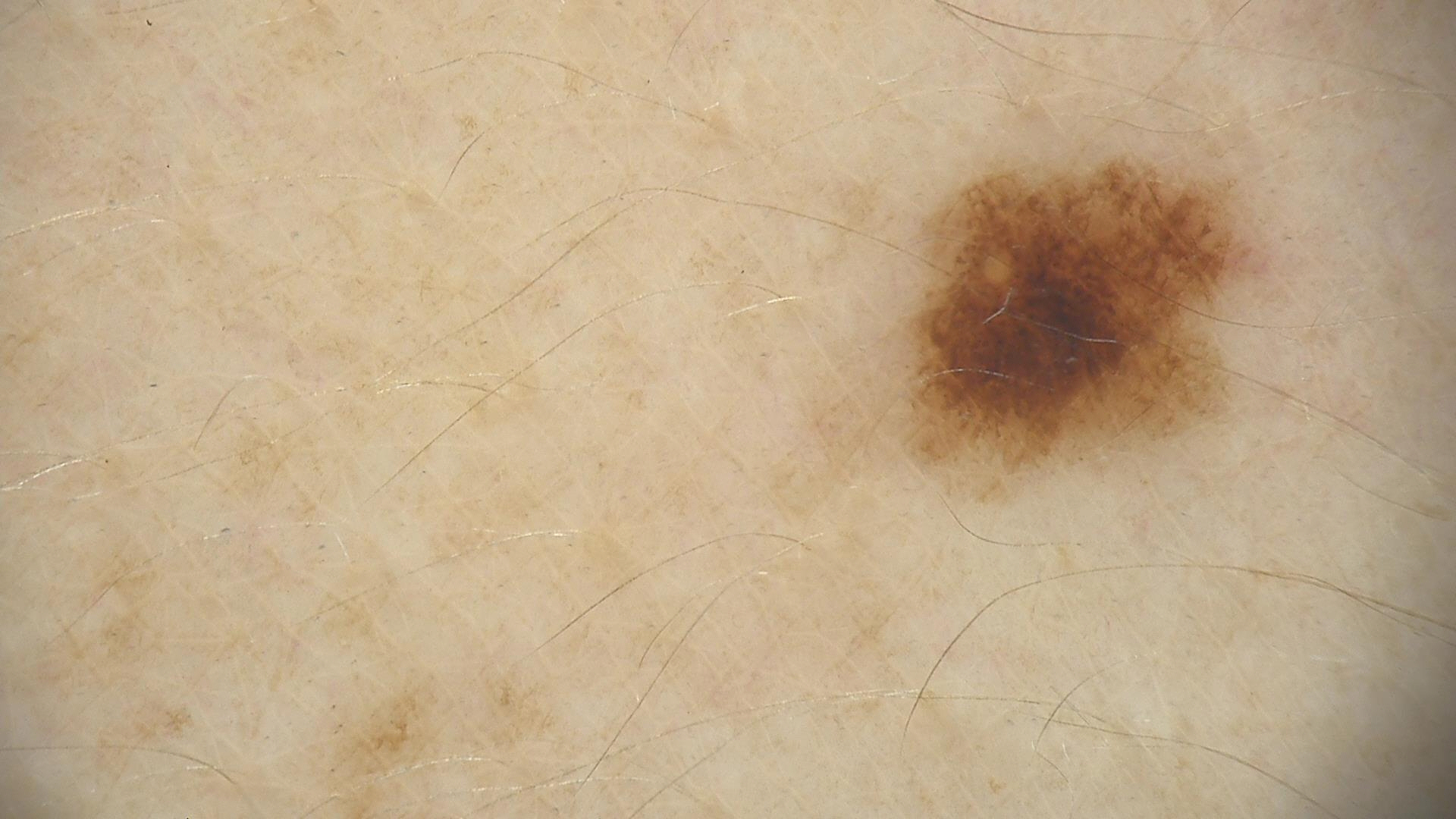Labeled as a dysplastic junctional nevus.